A male patient 72 years of age; imaged for a research study, with no referral diagnosis recorded; the patient says their skin tans without first burning; a clinical photograph showing a skin lesion.
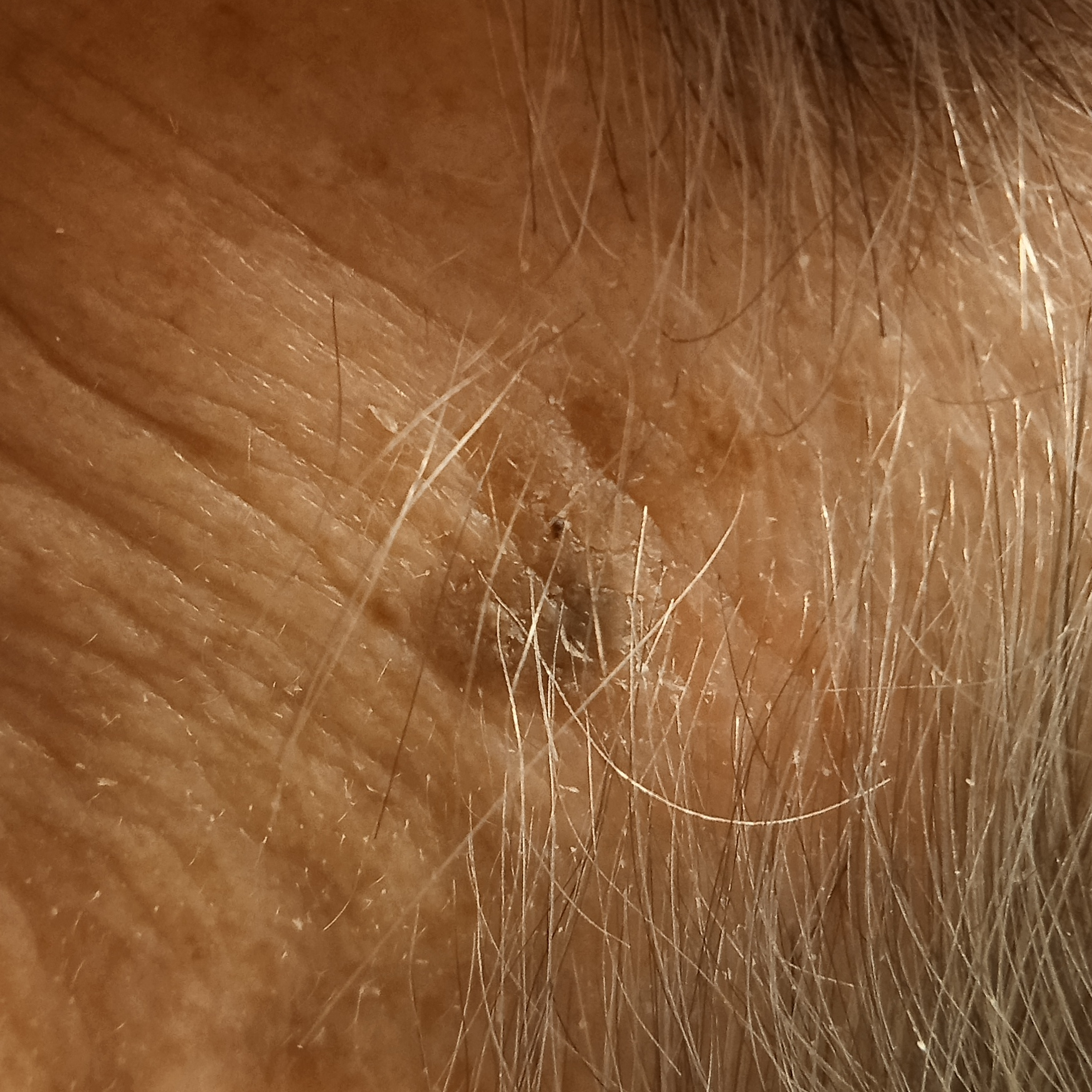Q: Where is the lesion?
A: an arm
Q: Lesion size?
A: 7.3 mm
Q: What was the diagnosis?
A: seborrheic keratosis (dermatologist consensus)